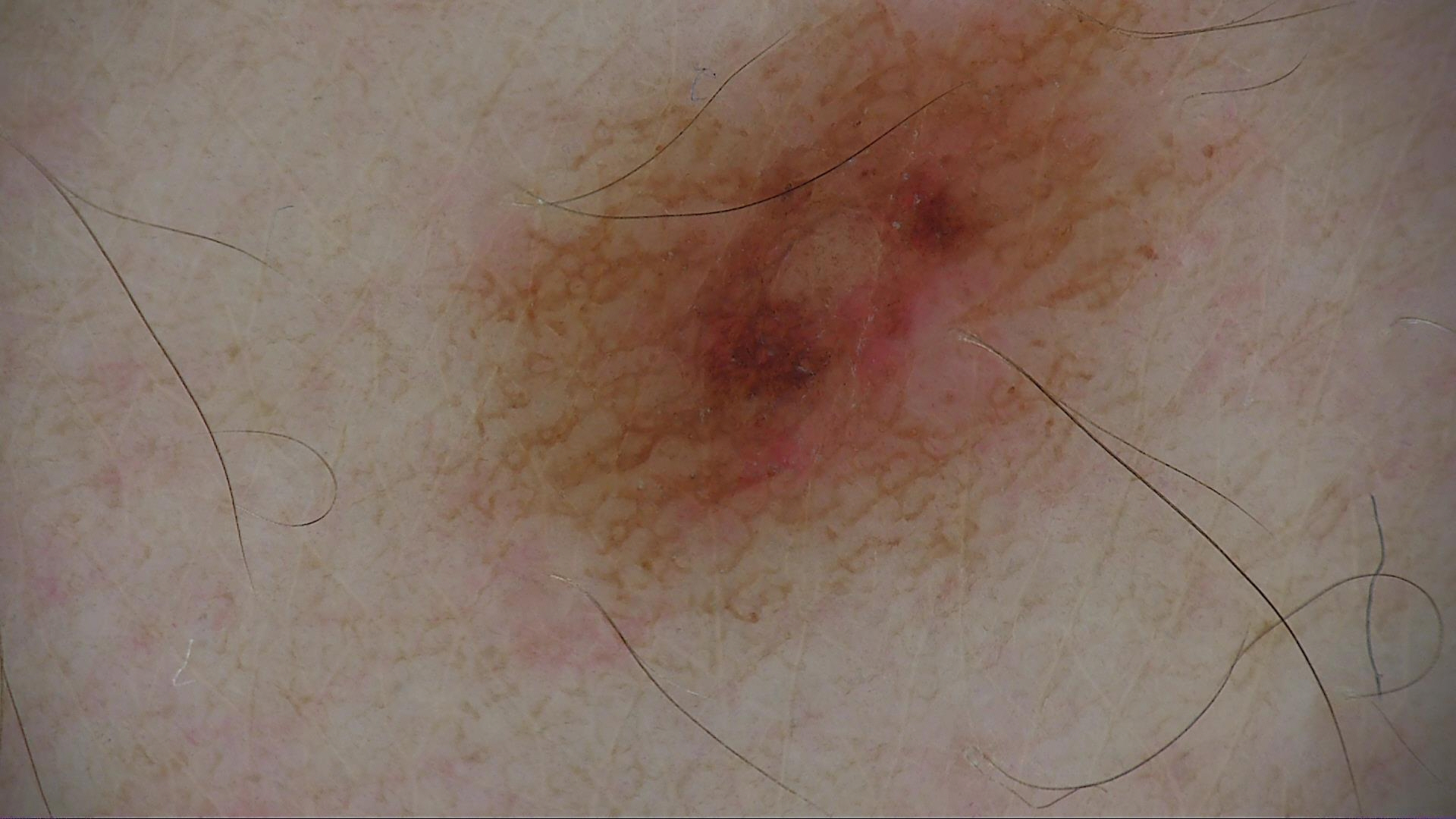modality = dermoscopy
diagnosis = dysplastic junctional nevus (expert consensus)